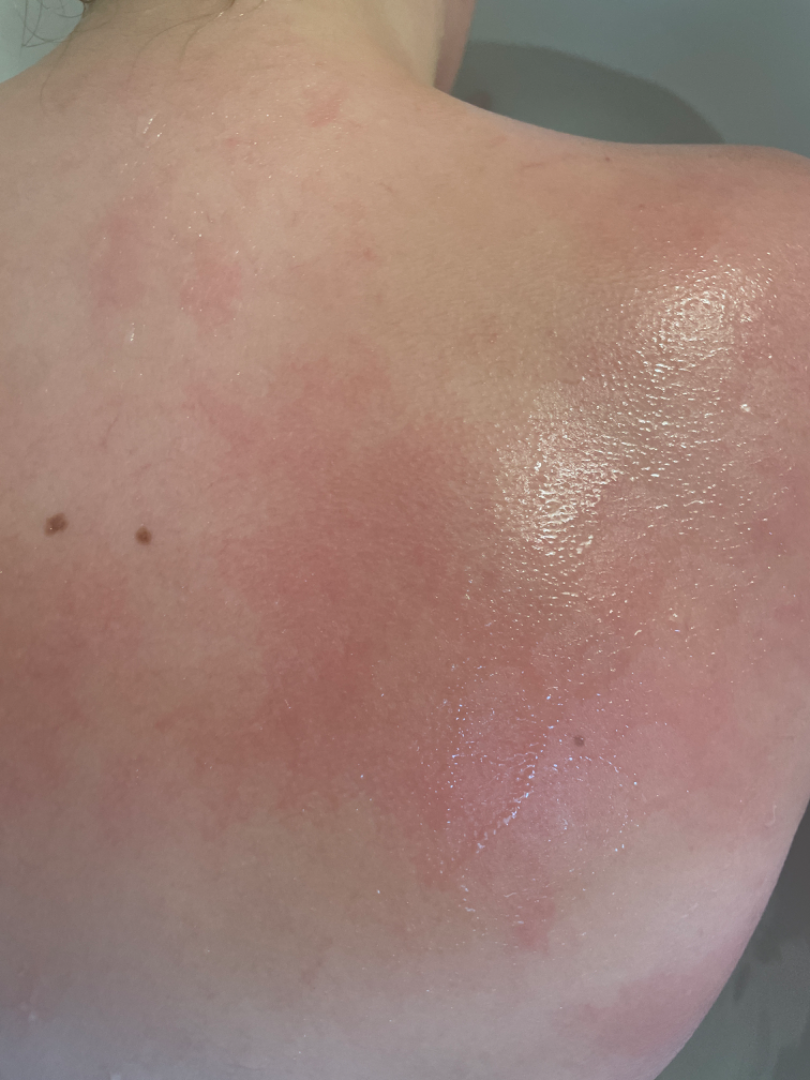Notes:
* differential: Hypersensitivity and Allergic Contact Dermatitis were each considered, in no particular order